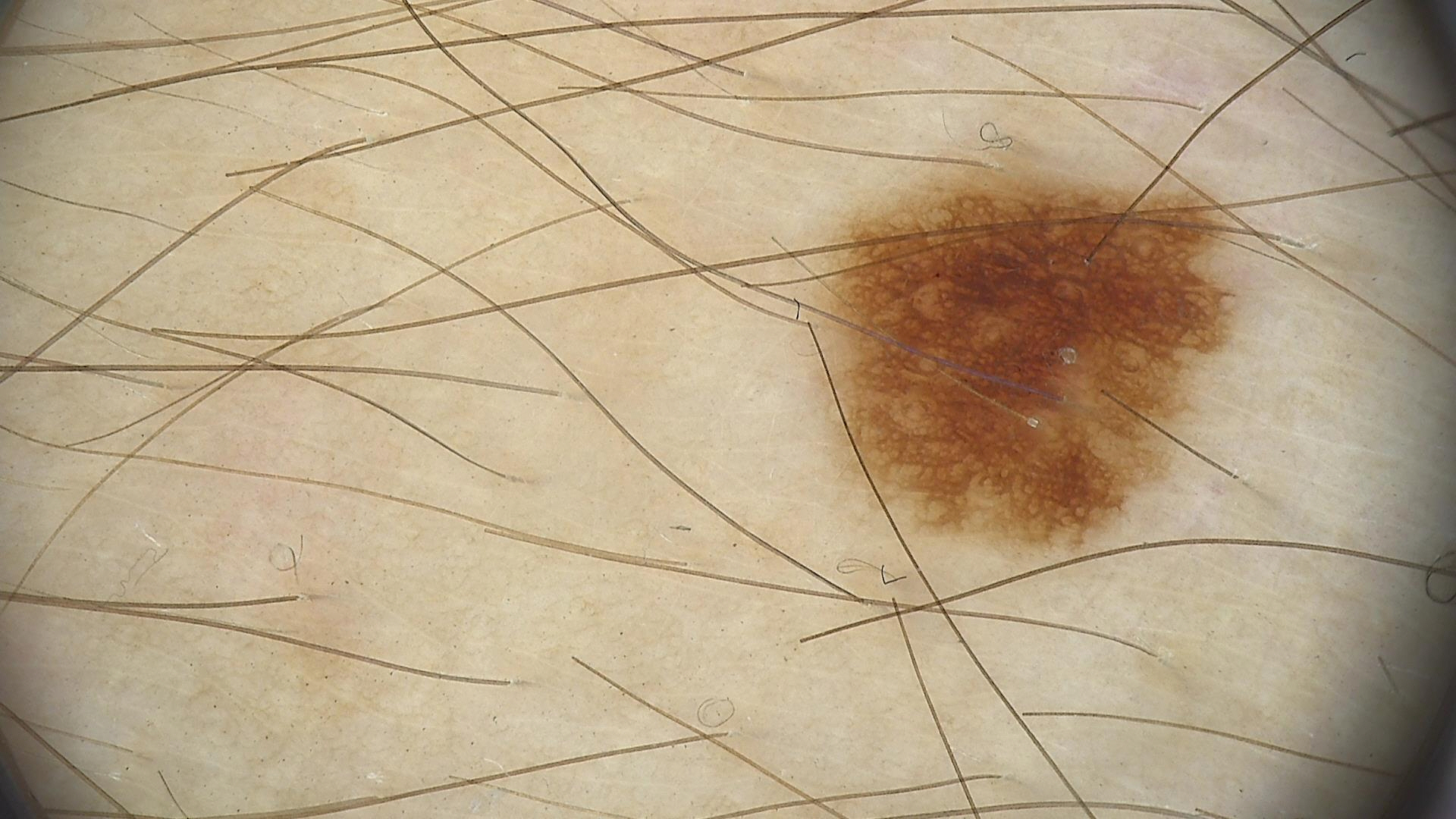Conclusion:
Diagnosed as a dysplastic junctional nevus.